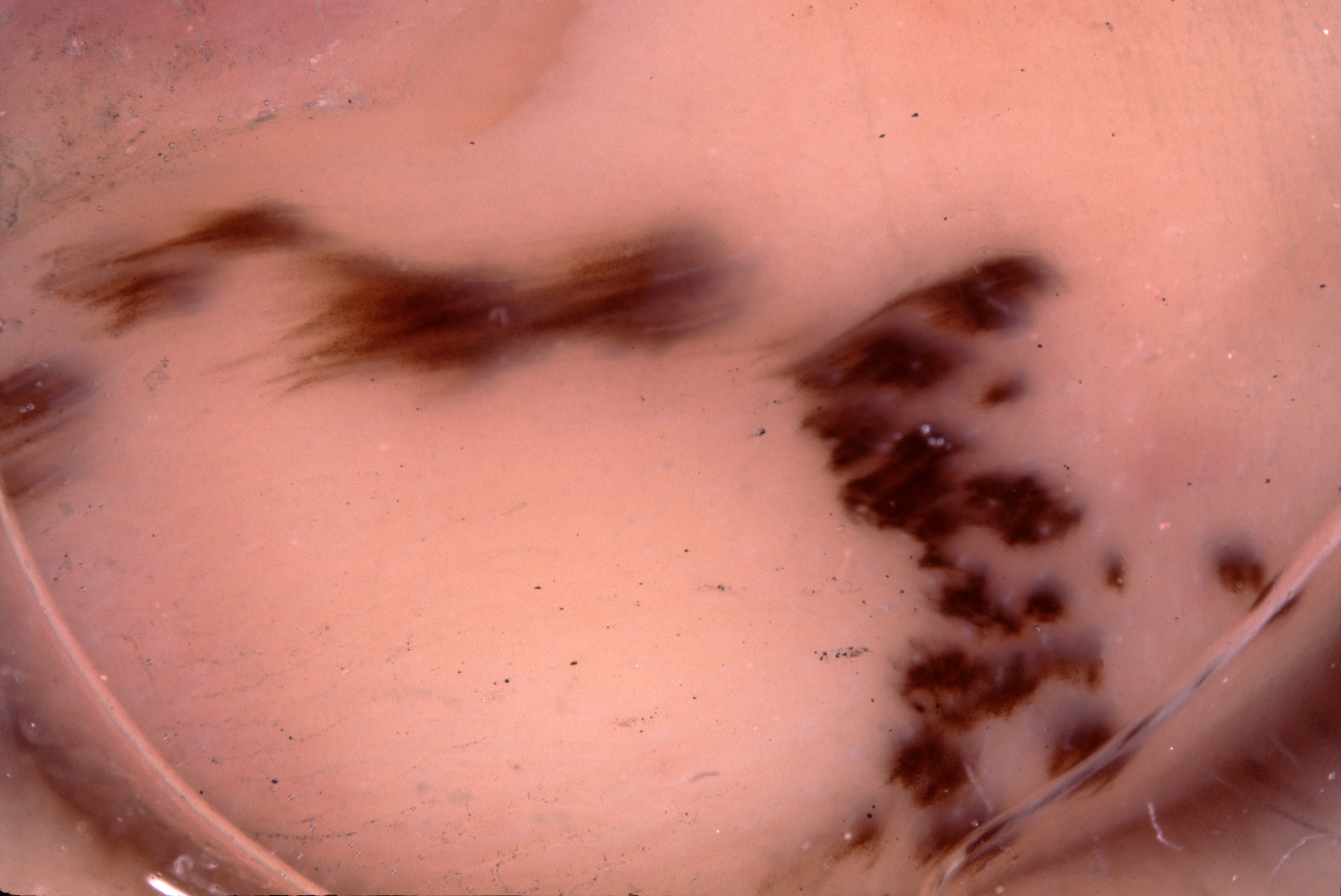{
  "image": {
    "modality": "dermoscopy"
  },
  "patient": {
    "sex": "female",
    "age_approx": 50
  },
  "dermoscopic_features": {
    "present": [],
    "absent": [
      "negative network",
      "pigment network",
      "milia-like cysts",
      "streaks"
    ]
  },
  "lesion_location": {
    "bbox_xyxy": [
      1,
      134,
      1333,
      894
    ]
  },
  "diagnosis": {
    "name": "melanocytic nevus",
    "malignancy": "benign",
    "lineage": "melanocytic",
    "provenance": "clinical"
  }
}